A skin lesion imaged with a dermatoscope; a female subject about 45 years old:
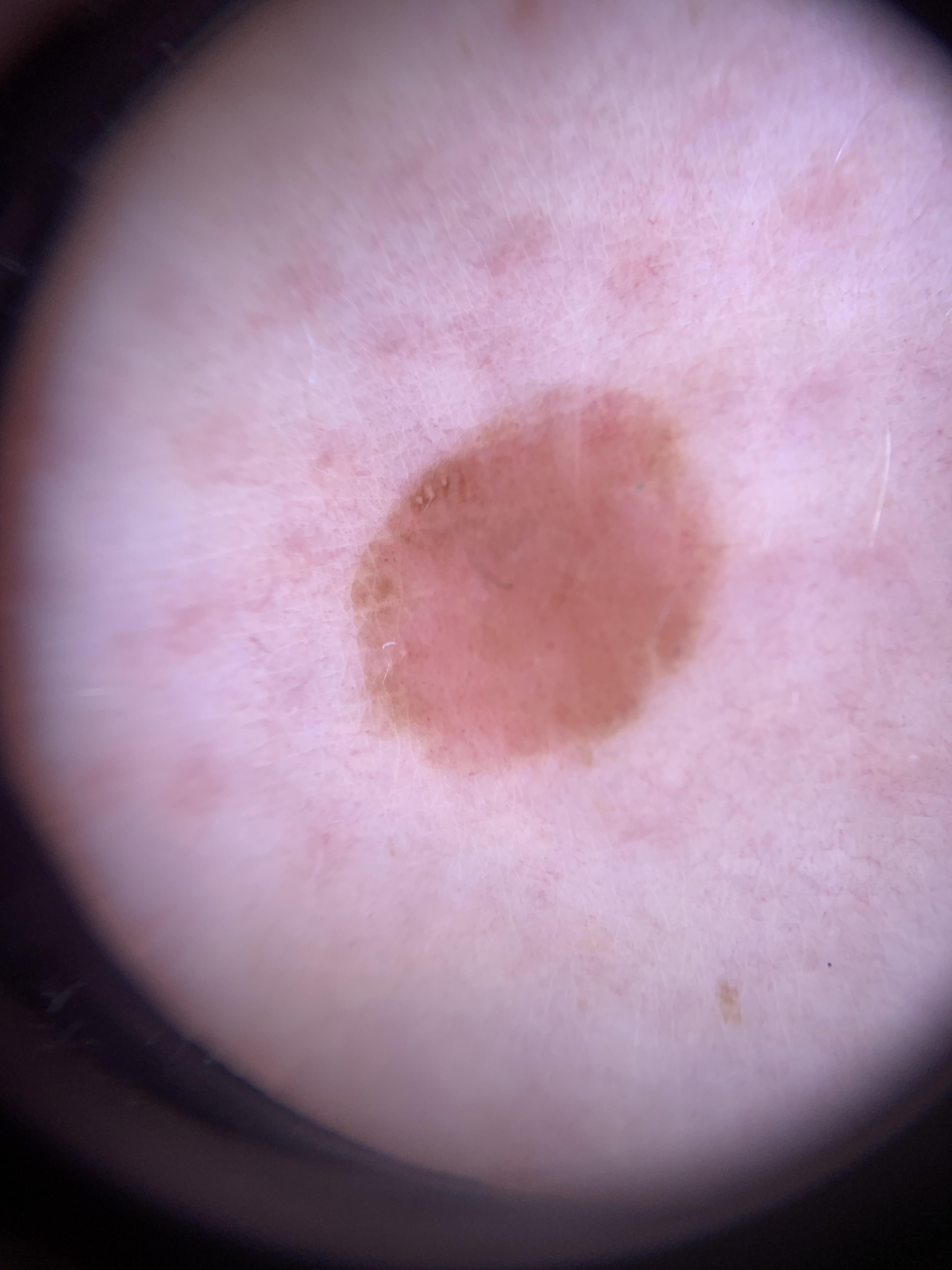Clinical context:
The lesion is on the trunk.
Conclusion:
Consistent with a nevus.